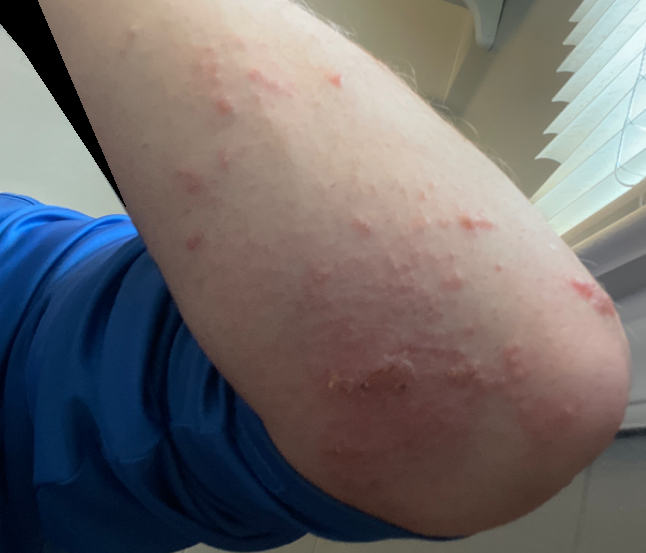| feature | finding |
|---|---|
| assessment | unable to determine |
| texture | raised or bumpy and fluid-filled |
| other reported symptoms | none reported |
| photo taken | close-up |
| duration | less than one week |
| contributor | male, age 18–29 |
| reported symptoms | itching, enlargement and burning |
| patient's own categorization | a rash |